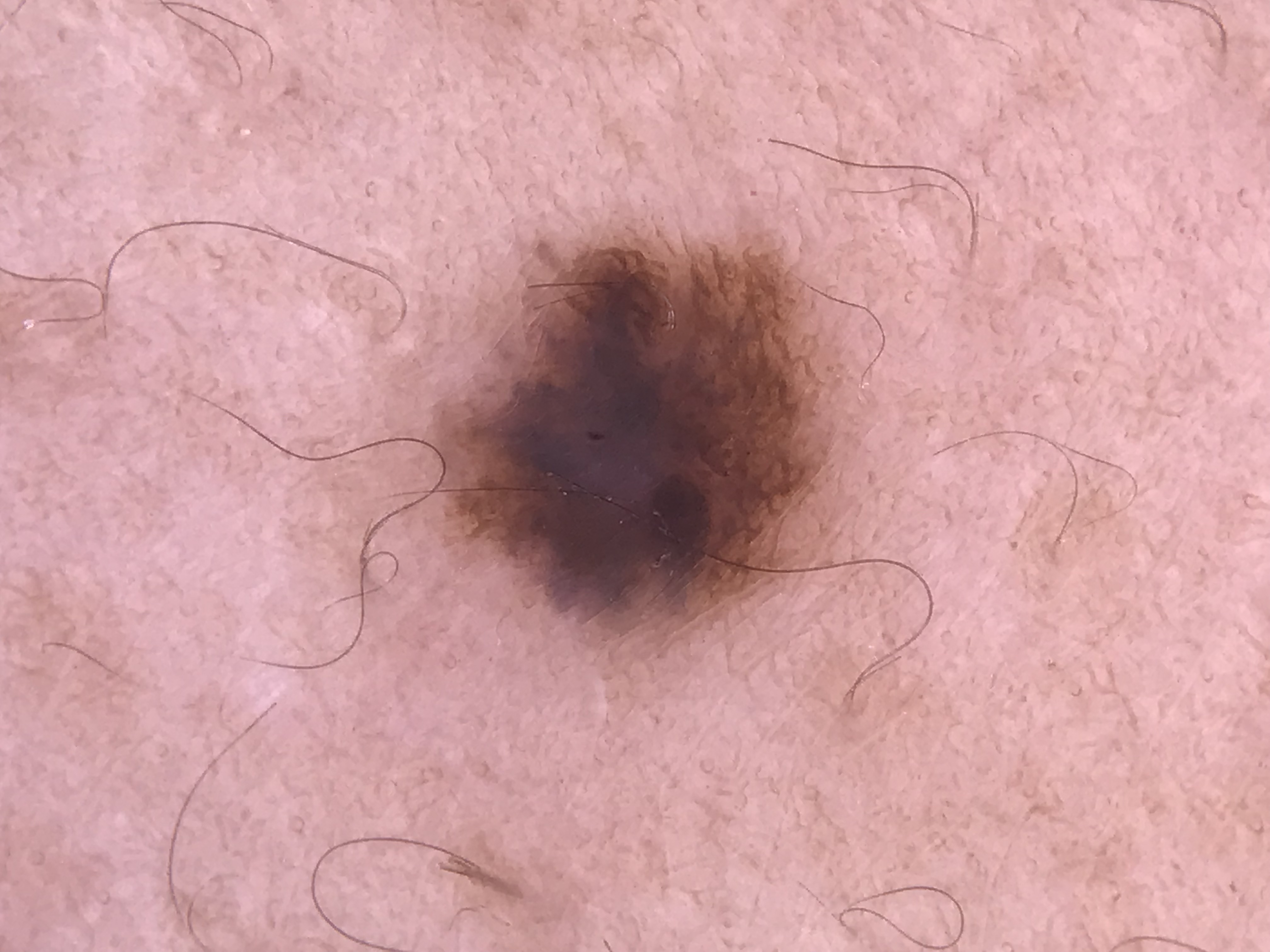Case:
– imaging · dermoscopy
– assessment · dysplastic compound nevus (expert consensus)